The leg and arm are involved. The photo was captured at a distance:
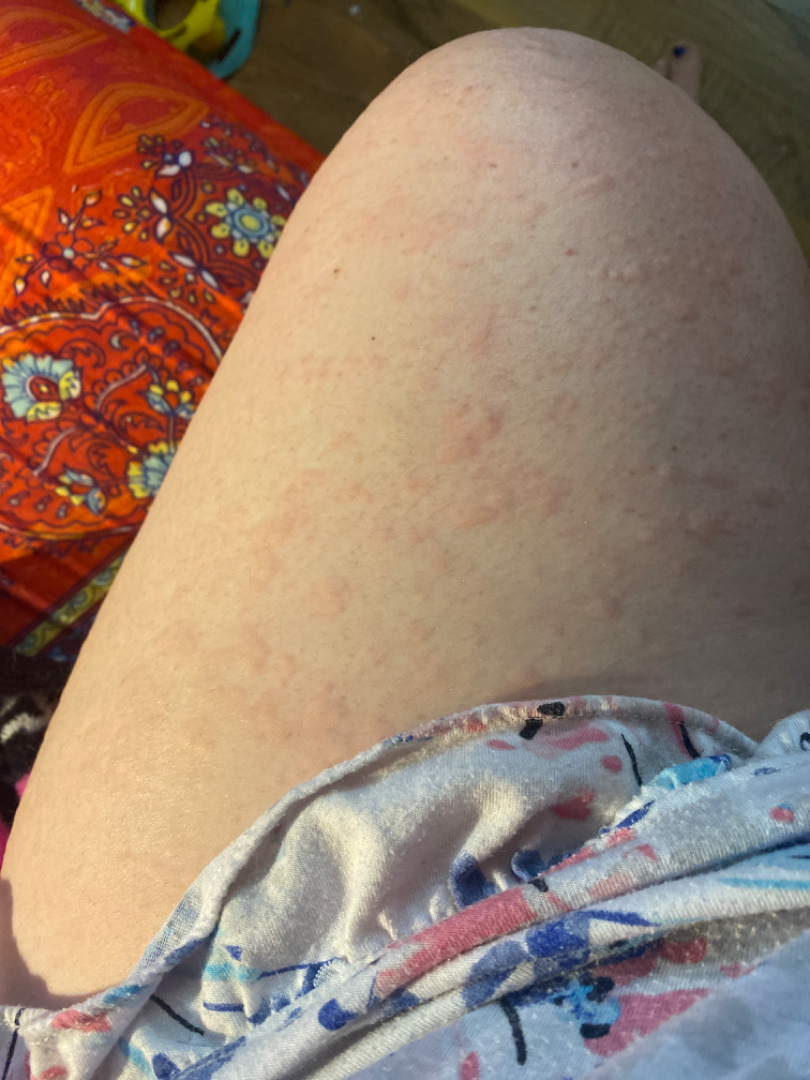Fitzpatrick skin type I; human graders estimated a Monk skin tone scale of 2.
The condition has been present for about one day.
The patient notes the lesion is raised or bumpy.
On photographic review by a dermatologist: favoring Urticaria; also raised was Eczema; less likely is Leukocytoclastic Vasculitis.